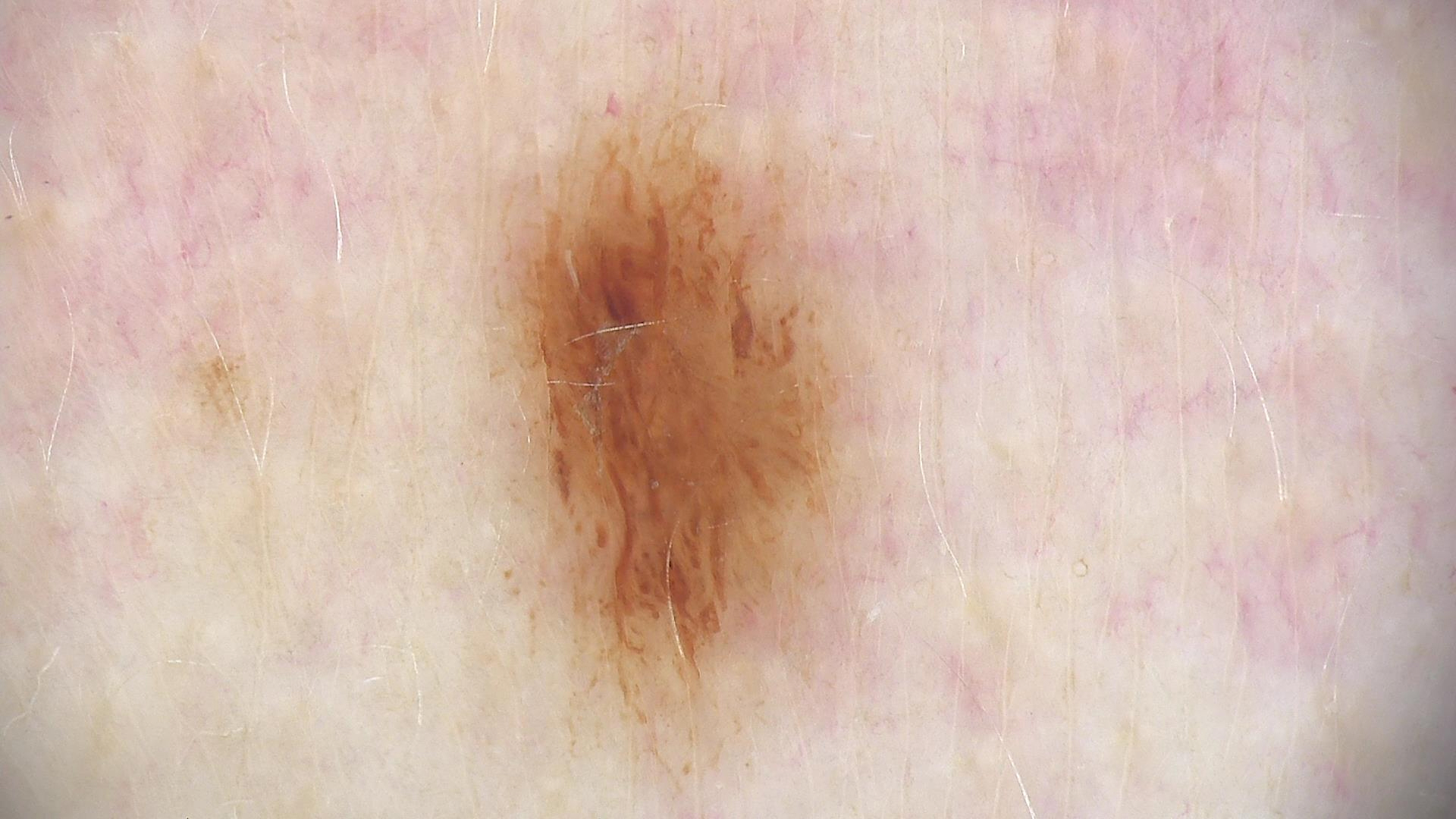<dermoscopy>
  <image>dermoscopy</image>
  <diagnosis>
    <name>dysplastic junctional nevus</name>
    <code>jd</code>
    <malignancy>benign</malignancy>
    <super_class>melanocytic</super_class>
    <confirmation>expert consensus</confirmation>
  </diagnosis>
</dermoscopy>